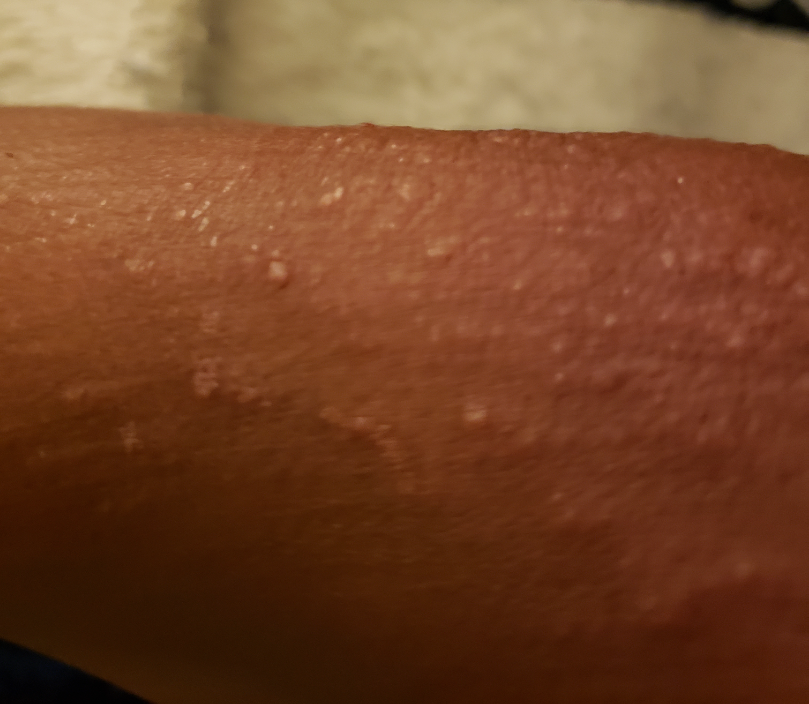patient = female, age 60–69
anatomic site = arm
self-categorized as = a rash
onset = less than one week
skin tone = Fitzpatrick phototype V; non-clinician graders estimated MST 4 or 6 (two reviewer pools disagreed)
framing = at an angle
lesion texture = raised or bumpy
impression = three dermatologists independently reviewed the case: the differential, in no particular order, includes Viral Exanthem, Hypersensitivity and Allergic Contact Dermatitis